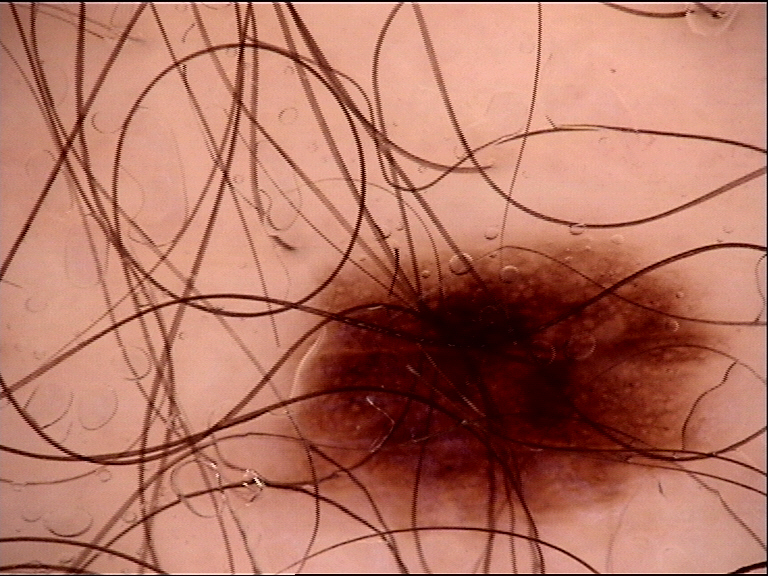Conclusion:
The diagnostic label was a benign lesion — a dysplastic junctional nevus.